Dermoscopy of a skin lesion.
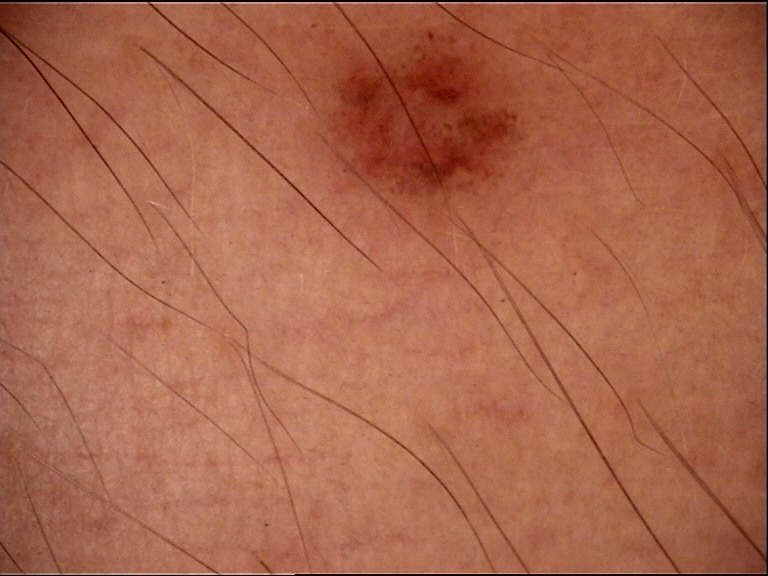Diagnosed as a benign lesion — a dysplastic junctional nevus.